The patient describes having few moles overall; the referring clinician suspected basal cell carcinoma; a male patient age 67; a clinical close-up of a skin lesion; the patient says their skin tans without first burning.
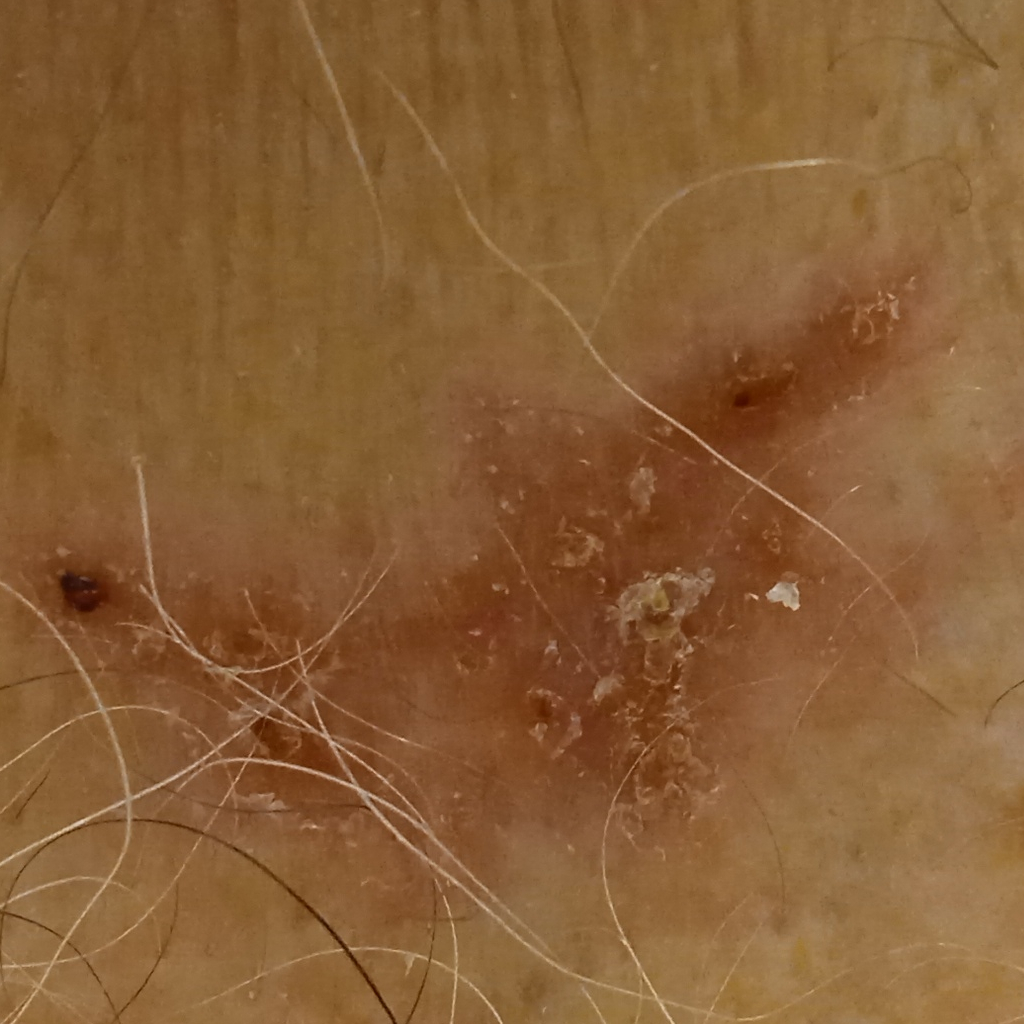Findings:
- anatomic site — the torso
- lesion size — 19 mm
- pathology — basal cell carcinoma (biopsy-proven)